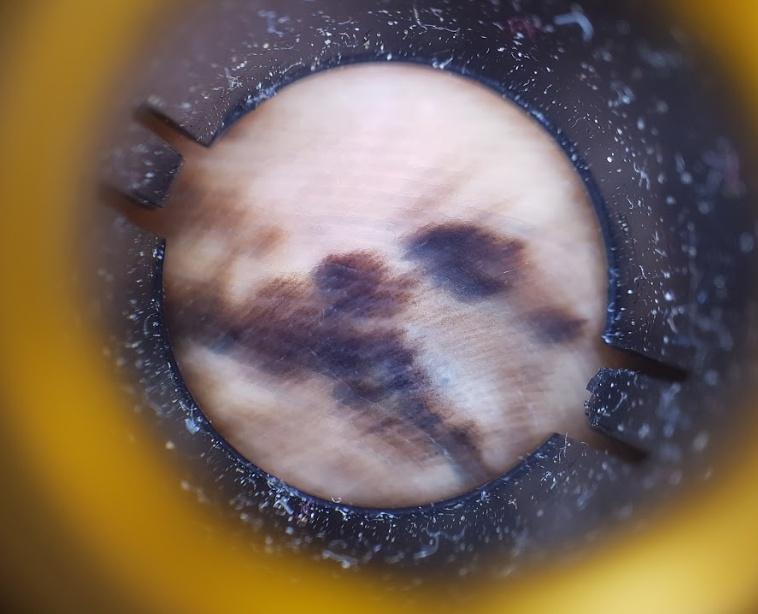<record>
<image>dermoscopic image</image>
<patient>
<age_approx>60</age_approx>
<sex>female</sex>
</patient>
<skin_type>II</skin_type>
<melanoma_history>
<personal_hx_melanoma>true</personal_hx_melanoma>
</melanoma_history>
<diagnosis>
<name>Melanoma</name>
<malignancy>malignant</malignancy>
<confirmation>histopathology</confirmation>
</diagnosis>
</record>